The subject is 50–59, male; the patient indicates pain and enlargement; the lesion involves the arm; the patient indicates the condition has been present for one to four weeks; self-categorized by the patient as a rash; no relevant systemic symptoms; the lesion is described as raised or bumpy; this is a close-up image: 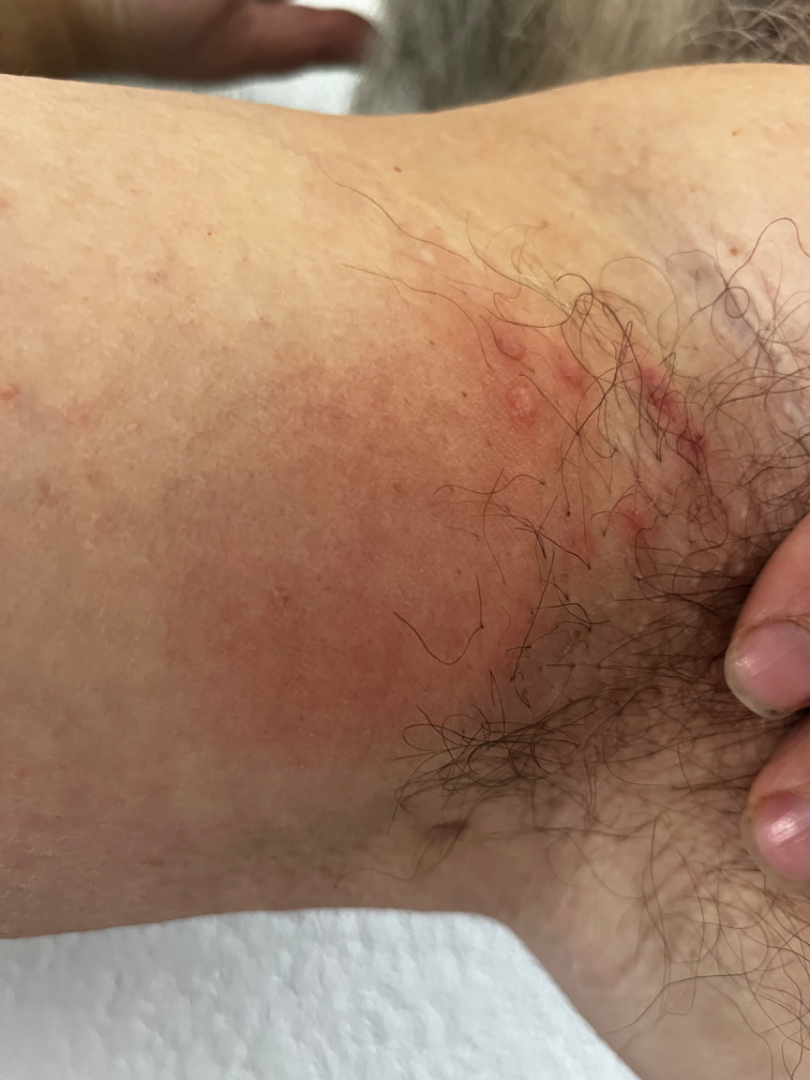| field | value |
|---|---|
| differential | Impetigo and Herpes Zoster were considered with similar weight; less probable is Allergic Contact Dermatitis |